This is a close-up image:
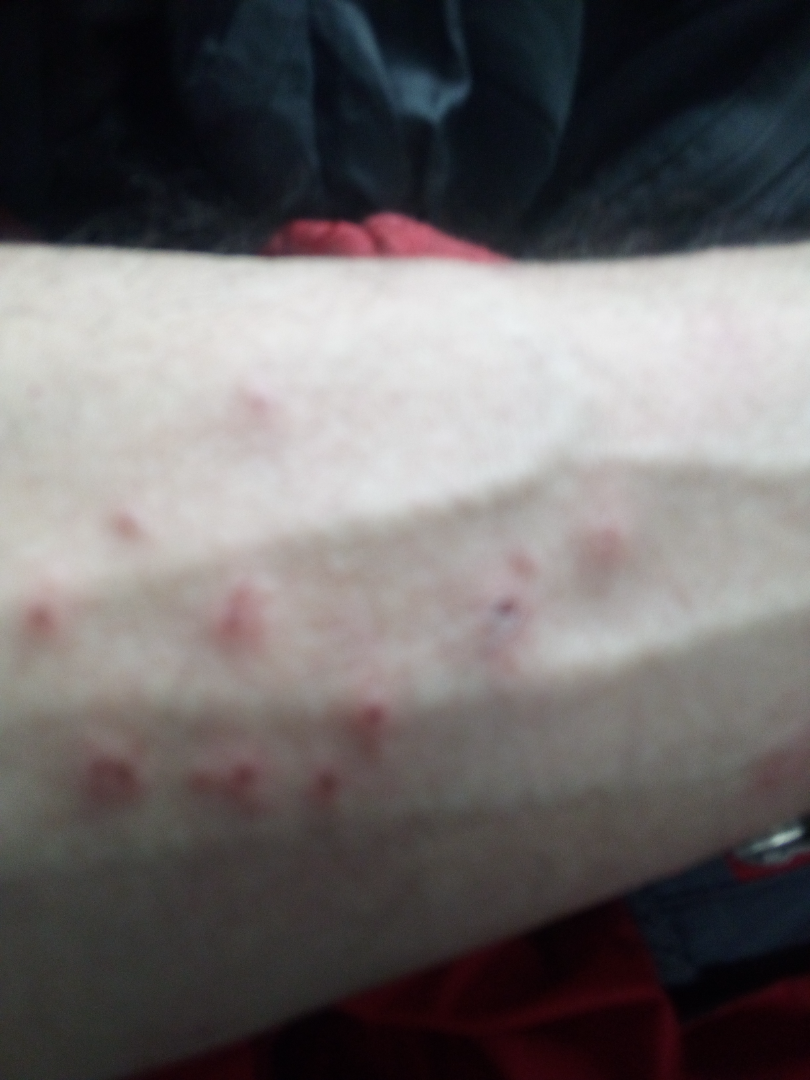Q: What conditions are considered?
A: Insect Bite and Allergic Contact Dermatitis were each considered, in no particular order